A dermoscopic image of a skin lesion: 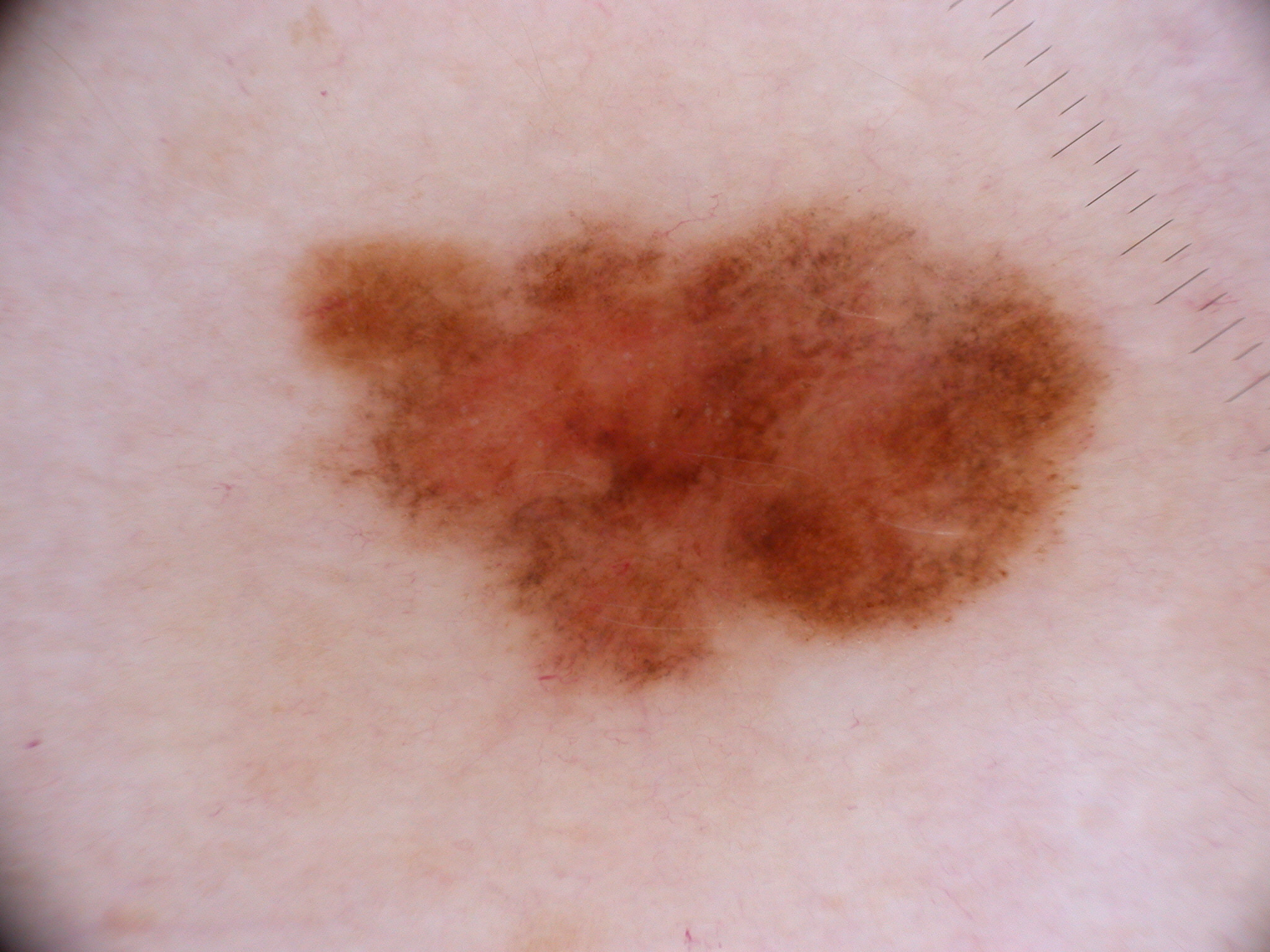  lesion_extent: moderate
  dermoscopic_features:
    present:
      - pigment network
    absent:
      - streaks
      - globules
      - milia-like cysts
      - negative network
  lesion_location:
    bbox_xyxy:
      - 290
      - 199
      - 1113
      - 710
  diagnosis:
    name: melanocytic nevus
    malignancy: benign
    lineage: melanocytic
    provenance: clinical